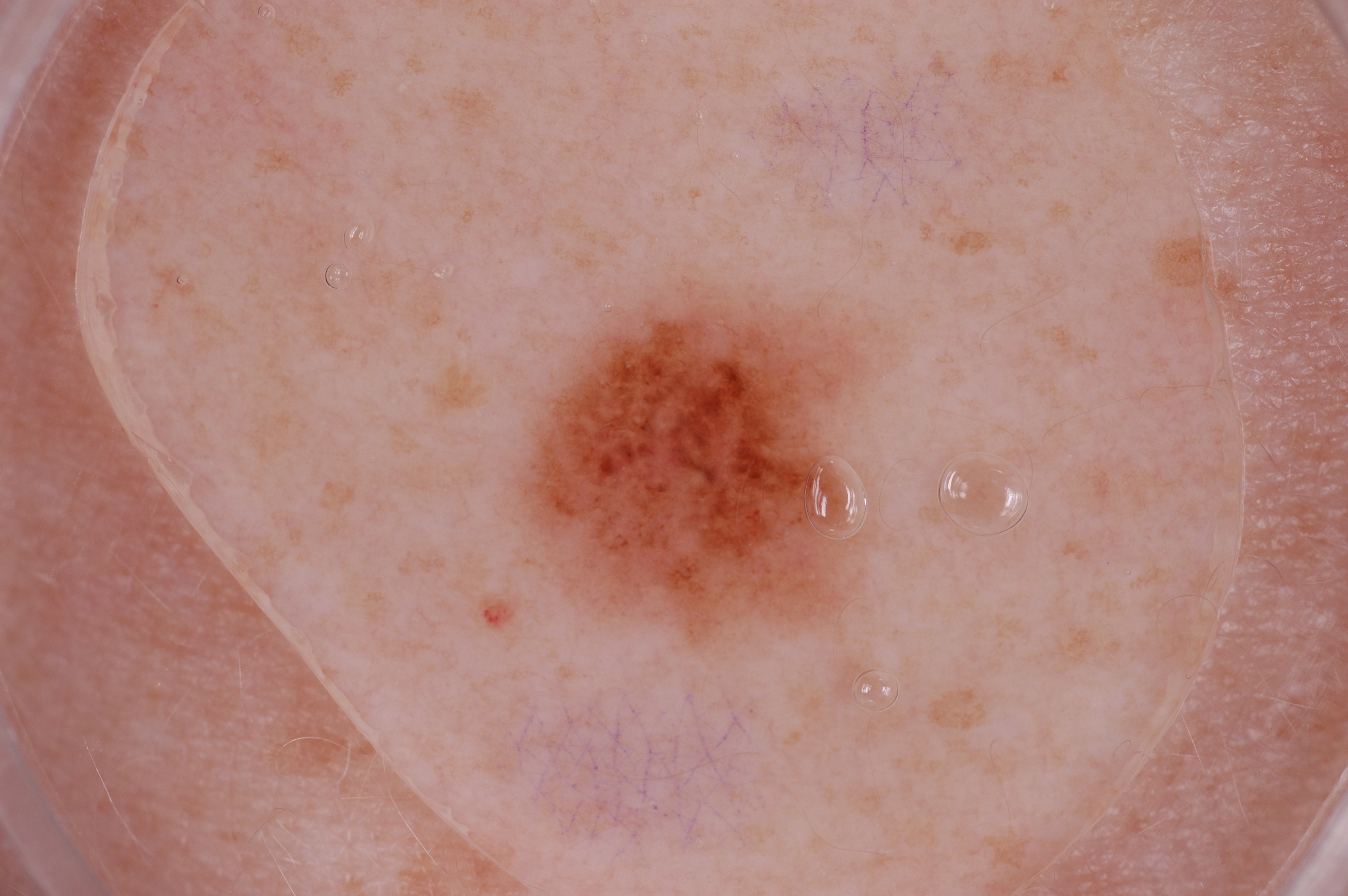<case>
  <patient>
    <sex>female</sex>
    <age_approx>40</age_approx>
  </patient>
  <image>
    <modality>dermoscopy</modality>
  </image>
  <lesion_location>
    <bbox_xyxy>527, 294, 863, 637</bbox_xyxy>
  </lesion_location>
  <dermoscopic_features>
    <present>pigment network</present>
    <absent>streaks, negative network, milia-like cysts</absent>
  </dermoscopic_features>
  <lesion_extent>
    <approx_field_fraction_pct>7</approx_field_fraction_pct>
  </lesion_extent>
  <diagnosis>
    <name>melanocytic nevus</name>
    <malignancy>benign</malignancy>
    <lineage>melanocytic</lineage>
    <provenance>clinical</provenance>
  </diagnosis>
</case>